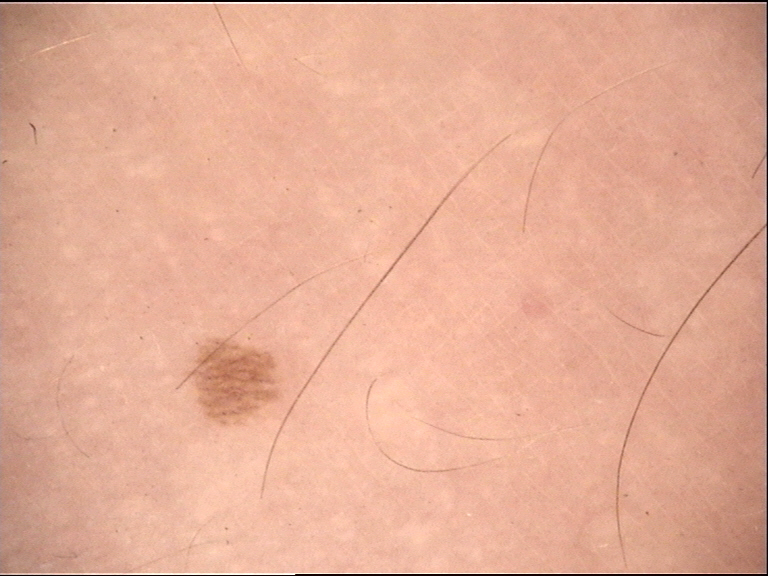{"diagnosis": {"name": "junctional nevus", "code": "jb", "malignancy": "benign", "super_class": "melanocytic", "confirmation": "expert consensus"}}